The photograph is a close-up of the affected area, present for less than one week, located on the leg, the lesion is associated with bothersome appearance, texture is reported as rough or flaky, skin tone: lay graders estimated a Monk Skin Tone of 2:
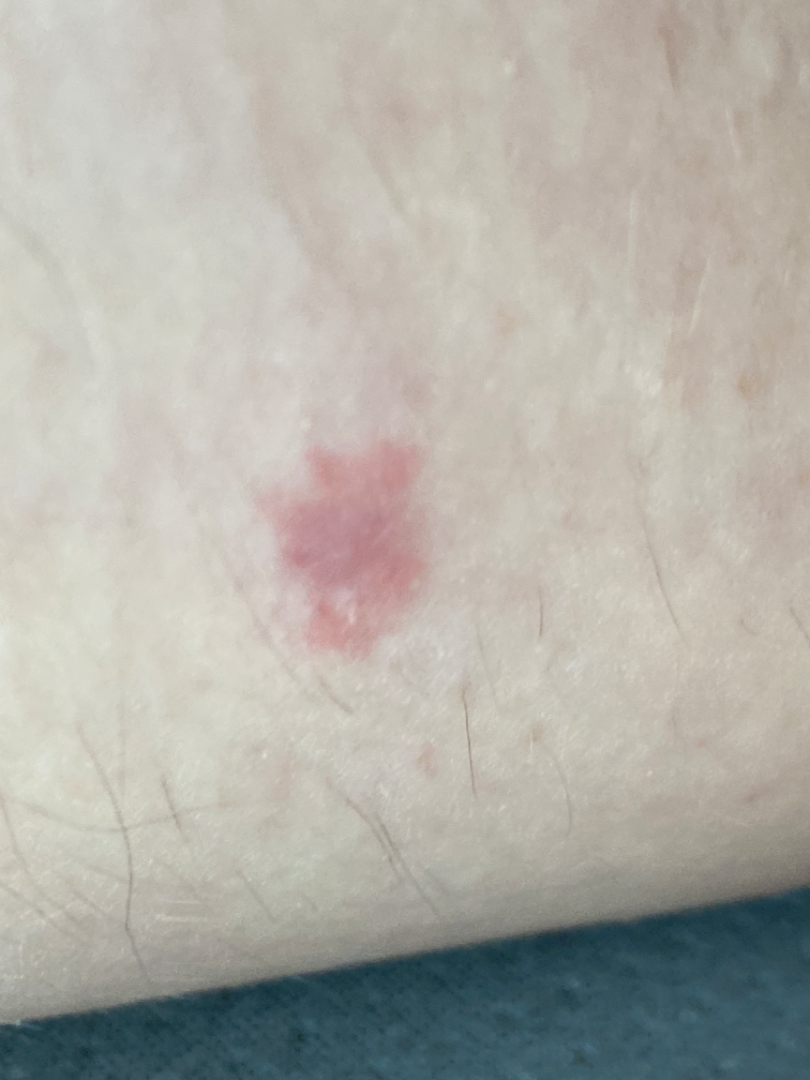Review: The dermatologist could not determine a likely condition from the photograph alone.